A dermoscopic close-up of a skin lesion: 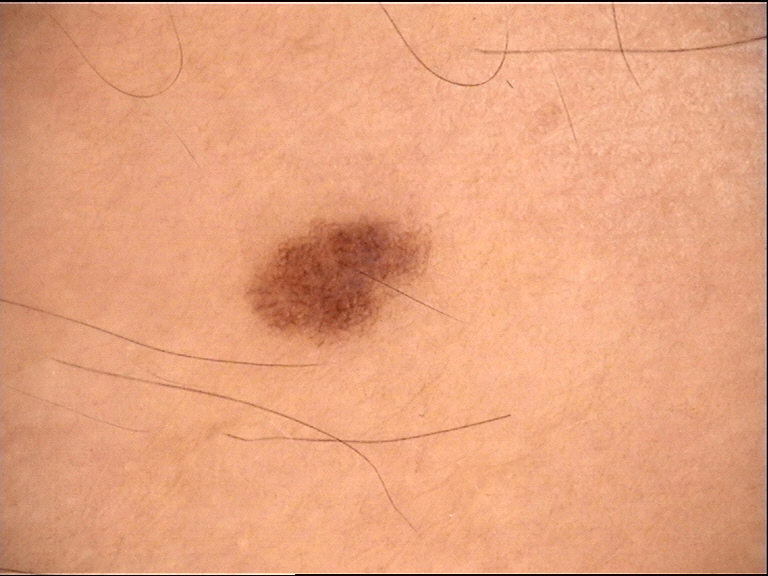Labeled as a dysplastic junctional nevus.